The photo was captured at a distance; the patient considered this a rash; the condition has been present for less than one week; the subject is a female aged 60–69; the lesion involves the leg; the contributor notes associated fatigue, mouth sores and joint pain; the lesion is described as fluid-filled and raised or bumpy.
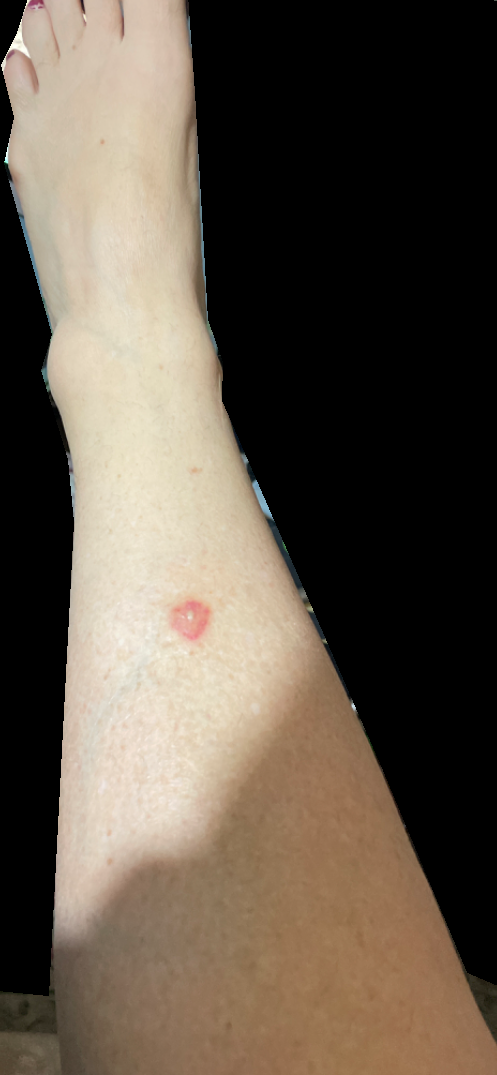differential: Insect Bite (favored).